The lesion involves the head or neck; the photograph was taken at an angle; the contributor is female.
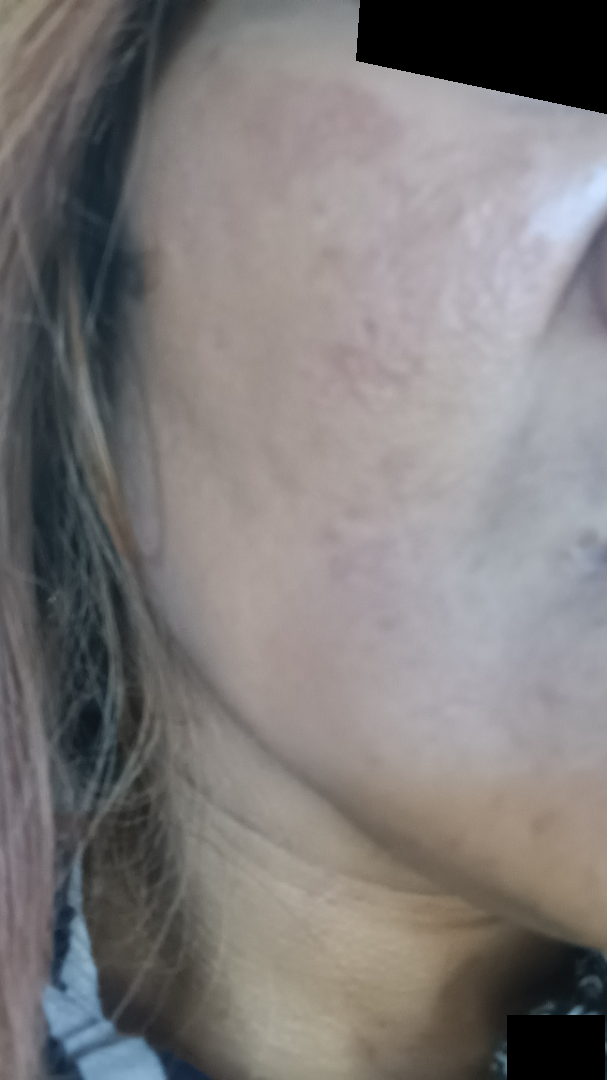dermatologist impression = Melasma, Scar Condition and Post-Inflammatory hyperpigmentation were each considered, in no particular order